The affected area is the top or side of the foot; no constitutional symptoms were reported; female patient, age 18–29; self-categorized by the patient as a rash; the photograph was taken at a distance; the patient reports burning, bothersome appearance and itching.
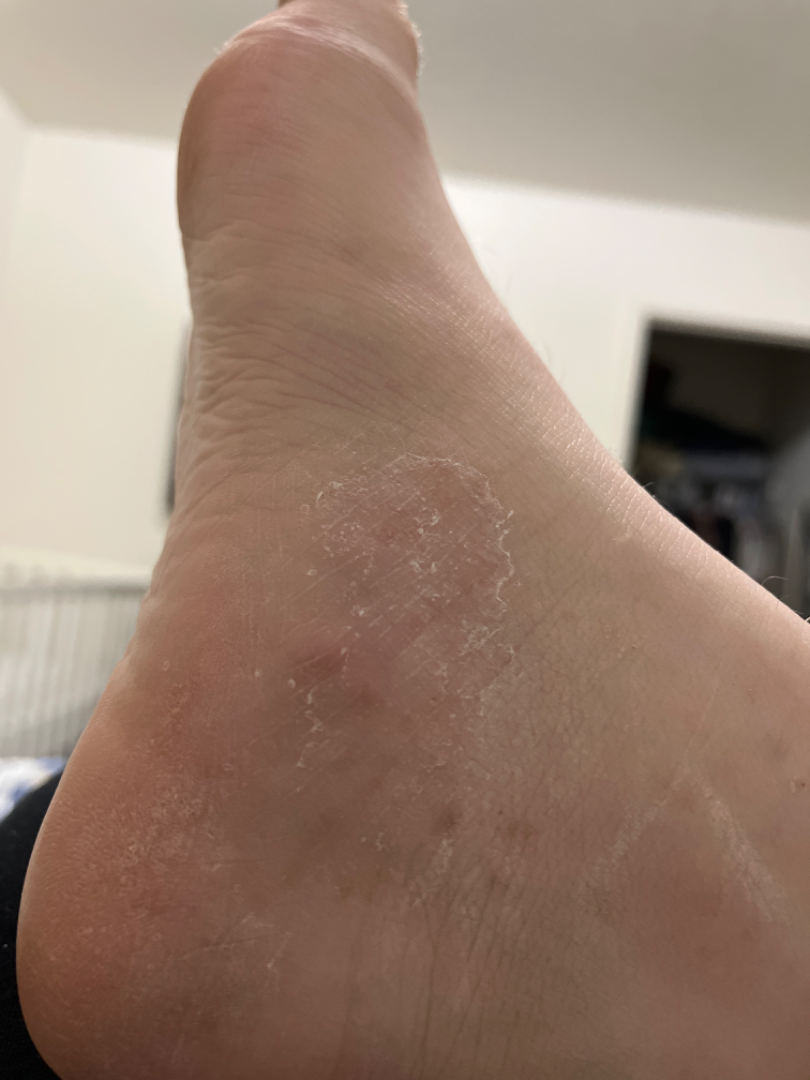{
  "assessment": "ungradable on photographic review"
}